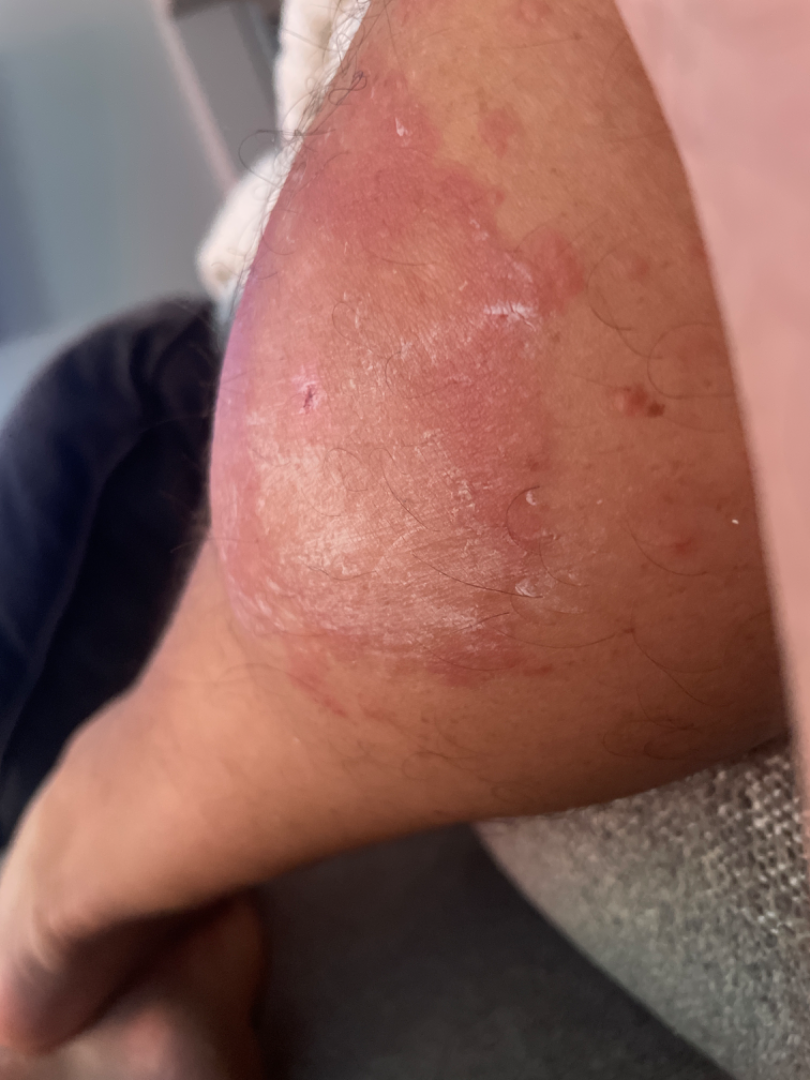The contributor reports enlargement and itching. The contributor reports the lesion is raised or bumpy. The contributor is male. Present for one to four weeks. The patient described the issue as a rash. This image was taken at an angle. Located on the leg. No relevant systemic symptoms. On remote review of the image, most consistent with Insect Bite; an alternative is Cellulitis; less likely is Abscess; a remote consideration is Fungal dermatosis; less probable is Cutaneous lyme disease.